The affected area is the arm · the patient notes burning, pain and itching · close-up view · the lesion is described as raised or bumpy and flat · the patient notes associated fatigue and joint pain · skin tone: FST IV; human graders estimated a Monk skin tone scale of 3 · present for more than one year · self-categorized by the patient as a rash · the contributor is a female aged 40–49 — 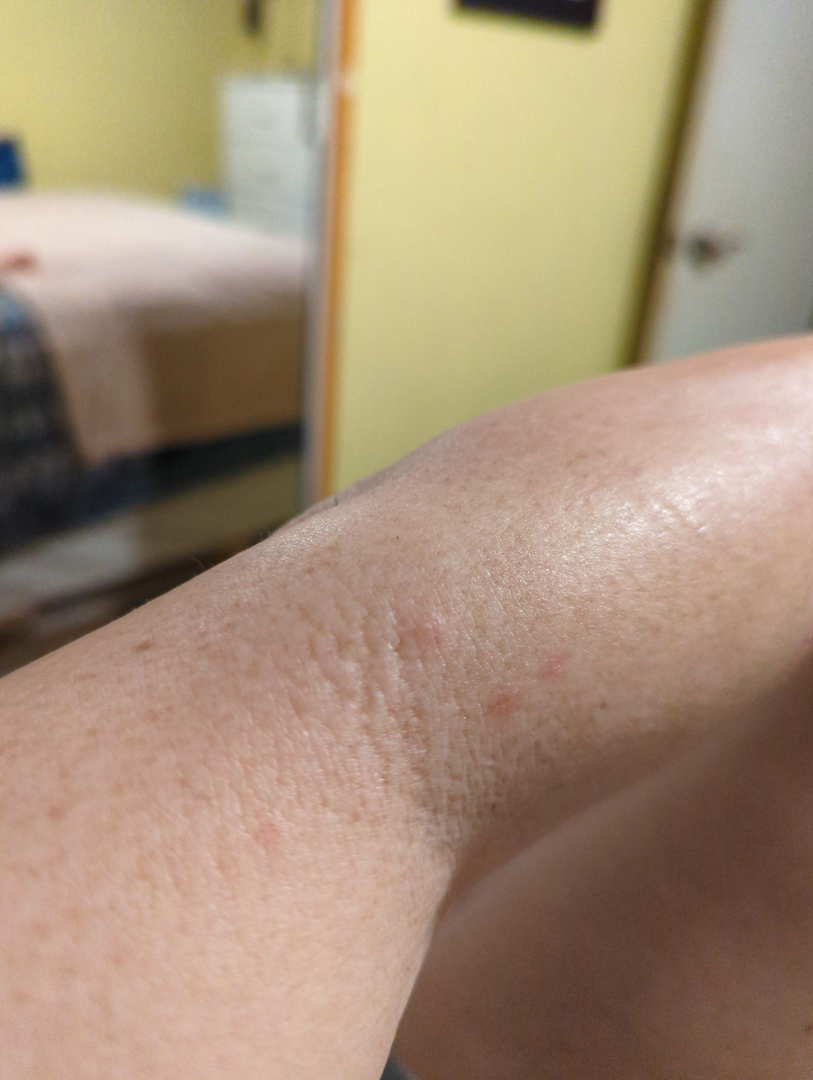The skin findings could not be characterized from the image.